The lesion is associated with itching; the patient reported no systemic symptoms; the subject is 30–39, male; present for more than one year; the leg is involved; texture is reported as raised or bumpy; close-up view:
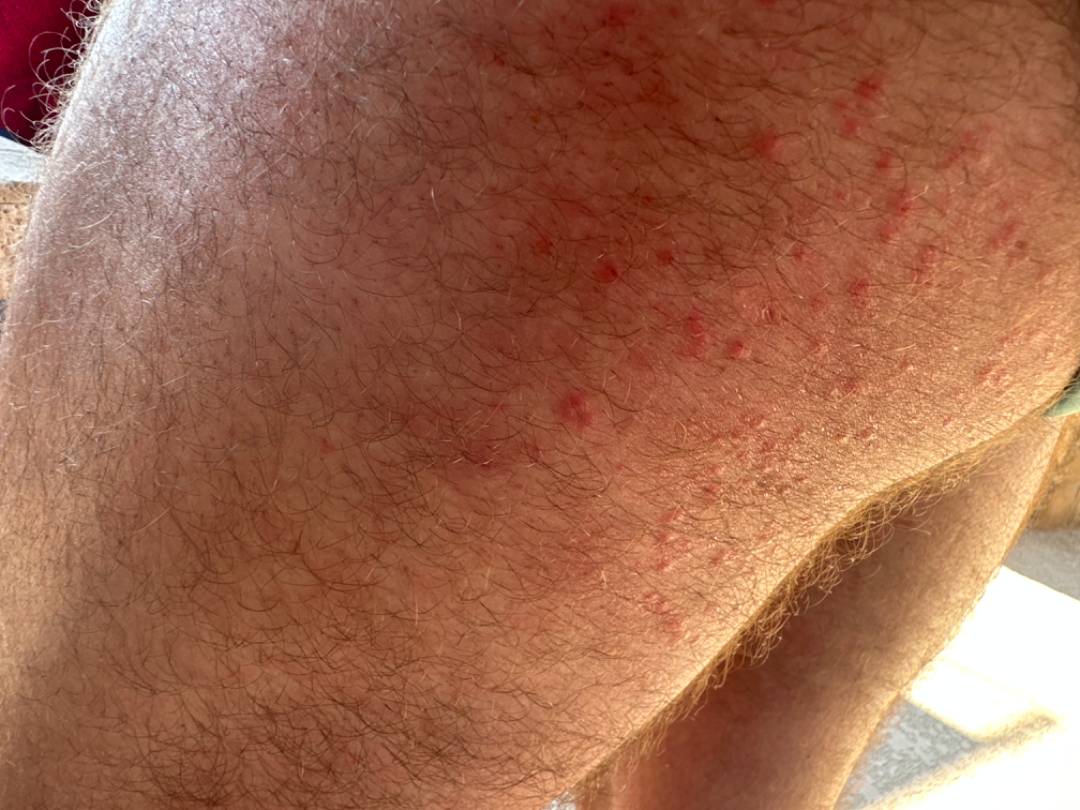Findings:
- assessment — ungradable on photographic review